A dermatoscopic image of a skin lesion.
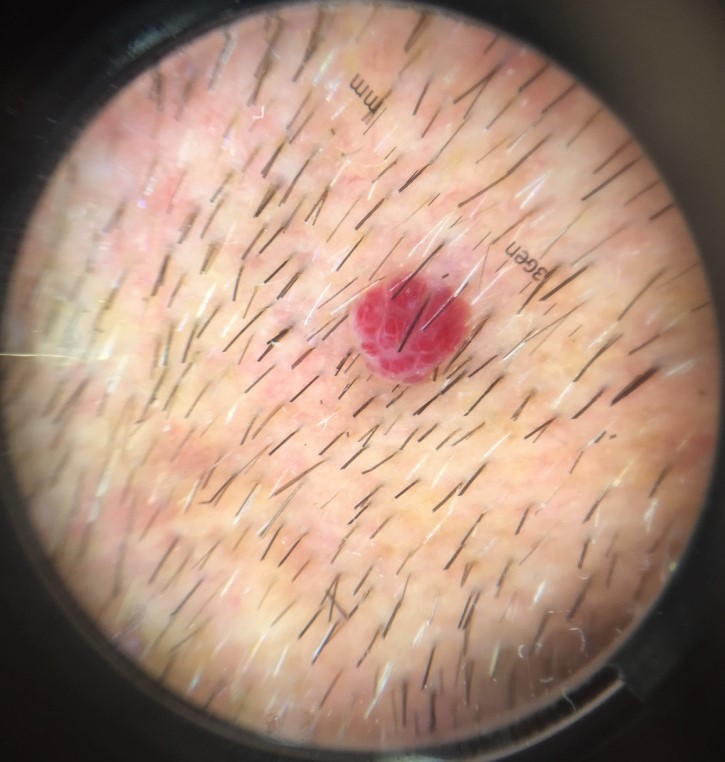Findings:
• label: hemangioma (expert consensus)